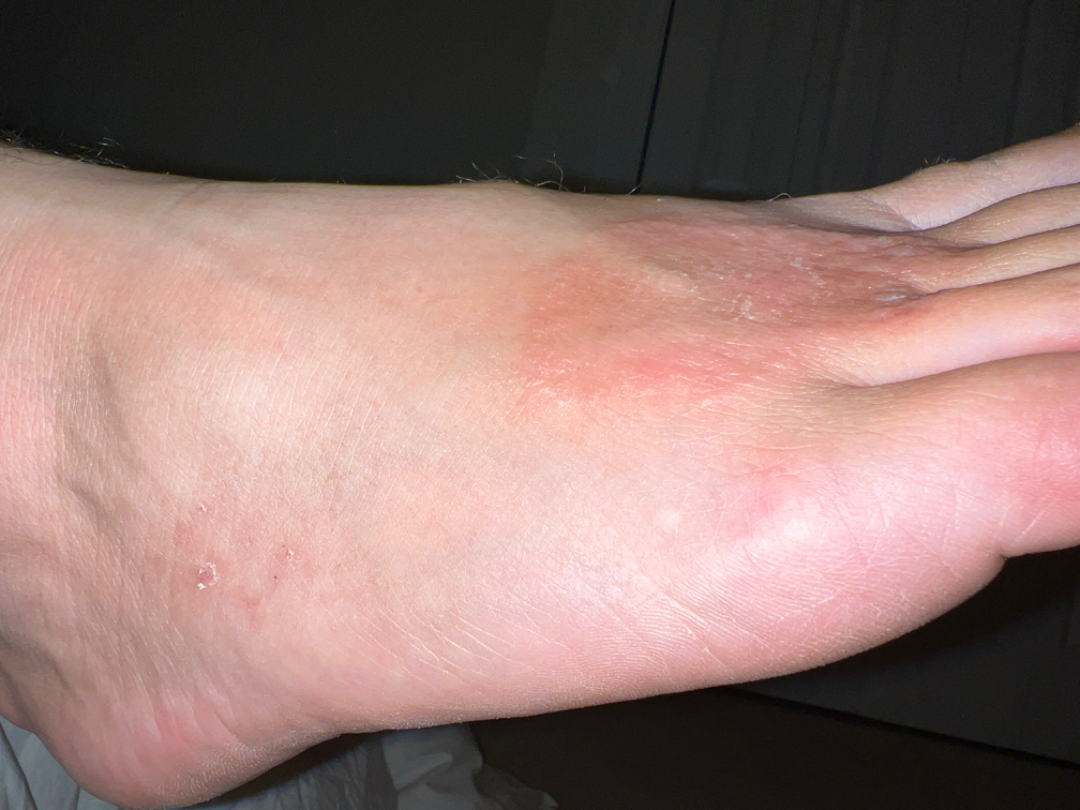Notes:
• symptom duration · one to four weeks
• patient-reported symptoms · none reported
• shot type · at an angle
• body site · top or side of the foot
• surface texture · raised or bumpy
• patient's own categorization · a rash
• skin tone · human graders estimated Monk skin tone scale 2 or 3
• clinical impression · Tinea (0.54); Psoriasis (0.23); Eczema (0.23)